A dermoscopic close-up of a skin lesion: 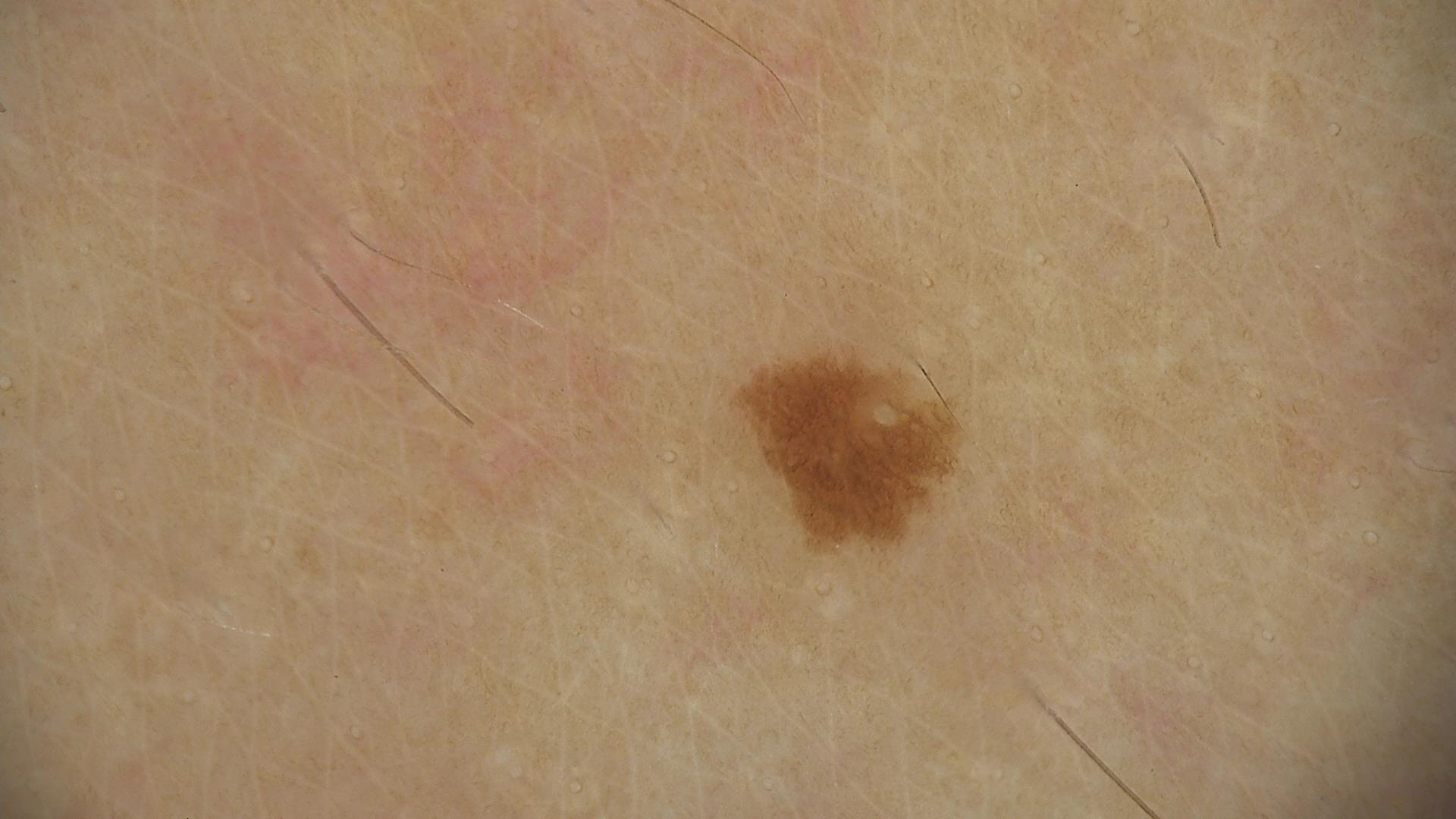classification: banal, label: junctional nevus (expert consensus).